A dermoscopy image of a single skin lesion.
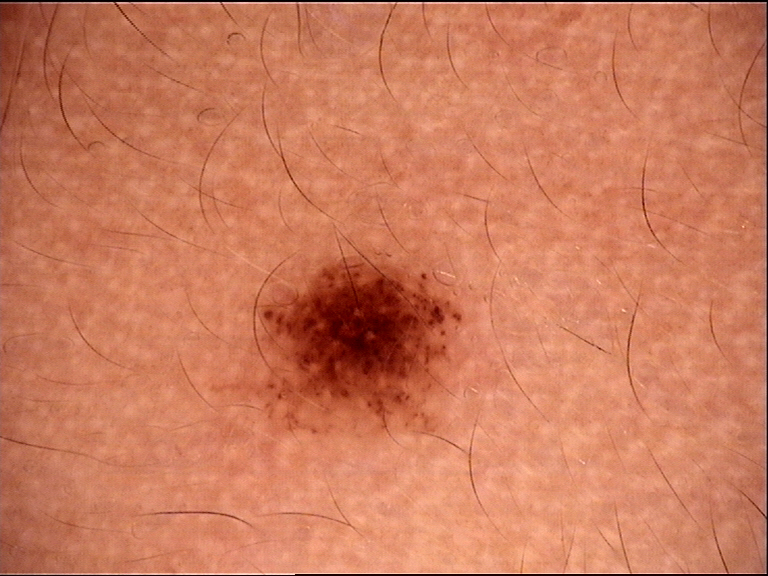| field | value |
|---|---|
| lesion type | compound, banal |
| class | Miescher nevus (expert consensus) |